Reported duration is about one day. Female patient, age 18–29. Symptoms reported: pain. The arm is involved. The lesion is described as raised or bumpy. The photograph was taken at a distance. The patient considered this acne.
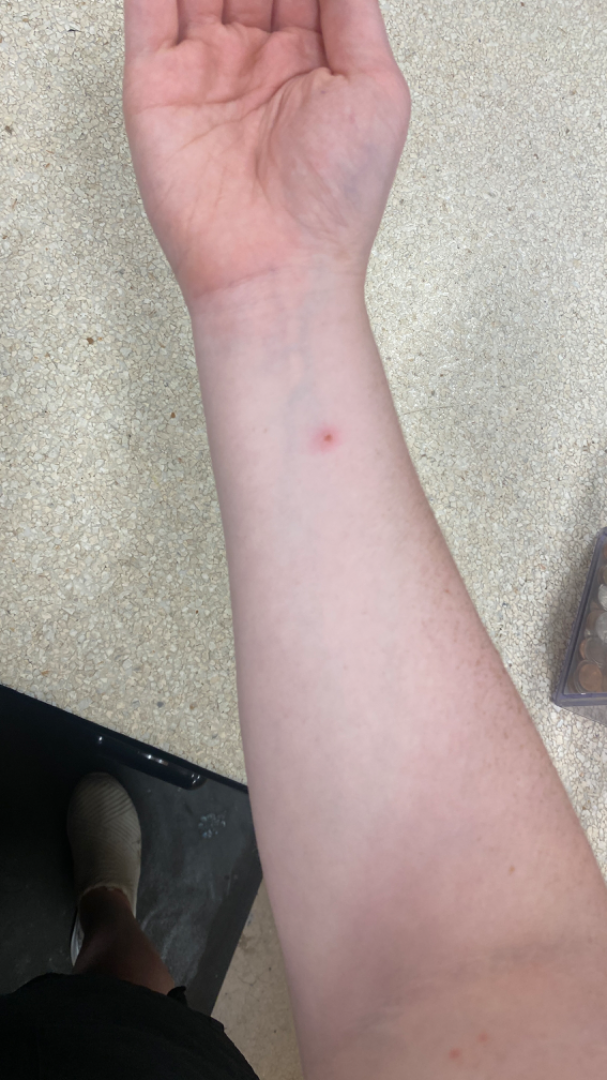* assessment: Impetigo and Insect Bite were each considered, in no particular order